The lesion involves the leg. Male subject, age 40–49. A close-up photograph: 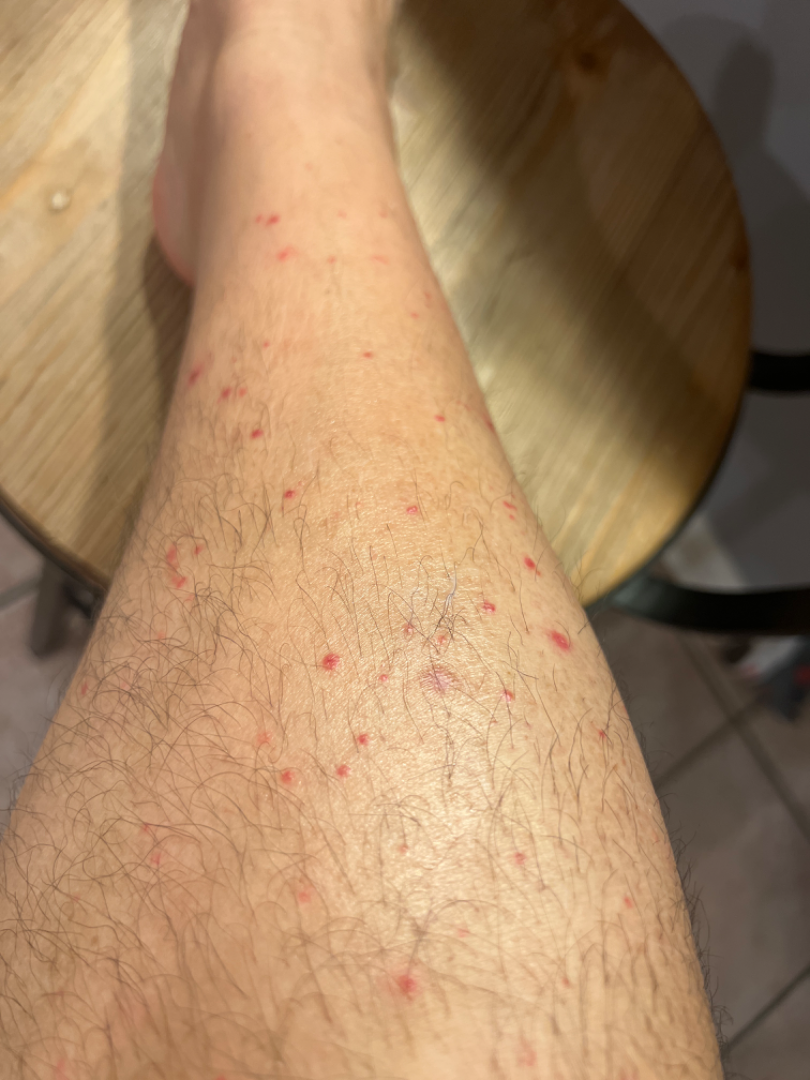Clinical context:
The patient considered this a rash. Reported duration is less than one week.
Assessment:
Favoring Leukocytoclastic Vasculitis; less likely is Drug Rash; lower on the differential is Scabies; less probable is Insect Bite; a remote consideration is Pigmented purpuric eruption.